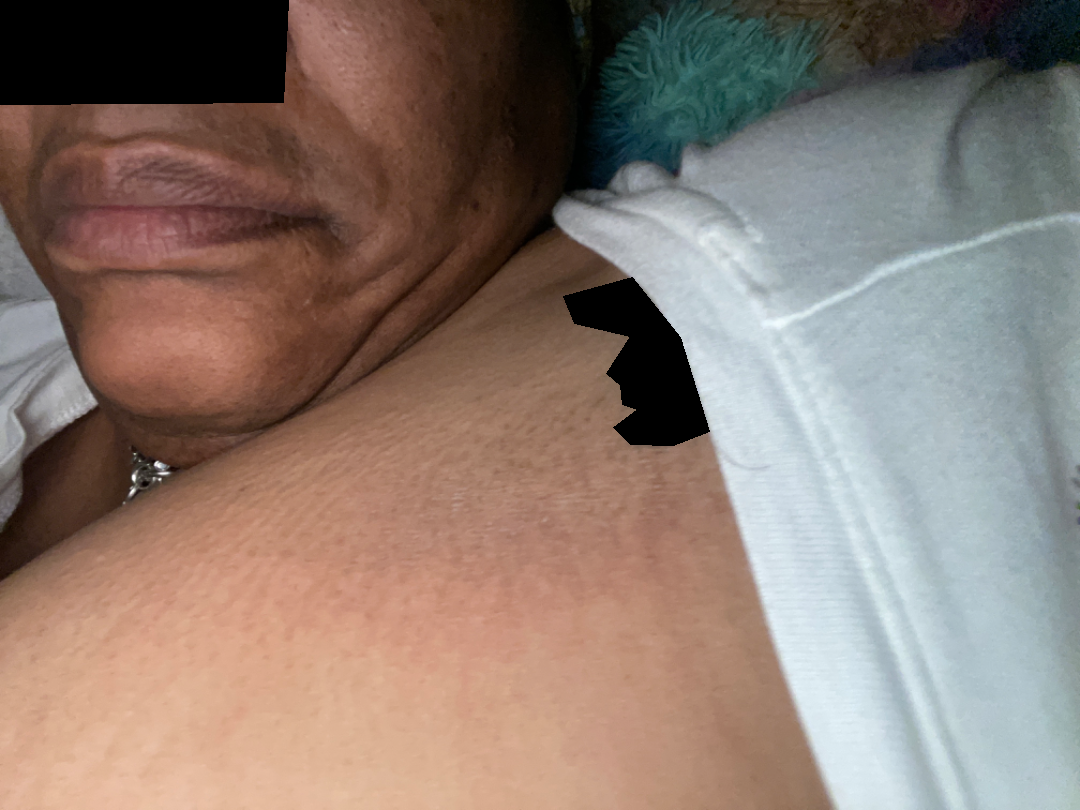Notes:
- assessment: could not be assessed
- body site: arm
- framing: close-up
- contributor: female, age 40–49